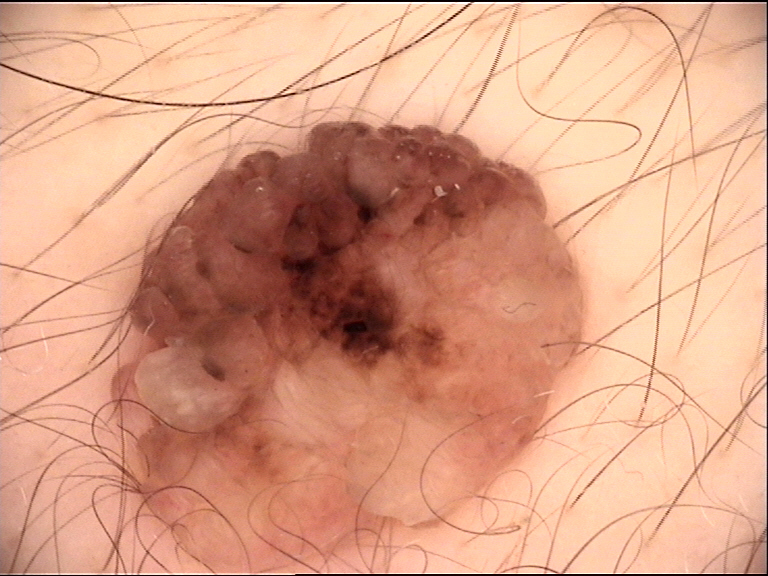A dermatoscopic image of a skin lesion. Consistent with a banal lesion — a dermal nevus.